The lesion involves the leg and arm · the photograph was taken at a distance · the contributor is a male aged 18–29: 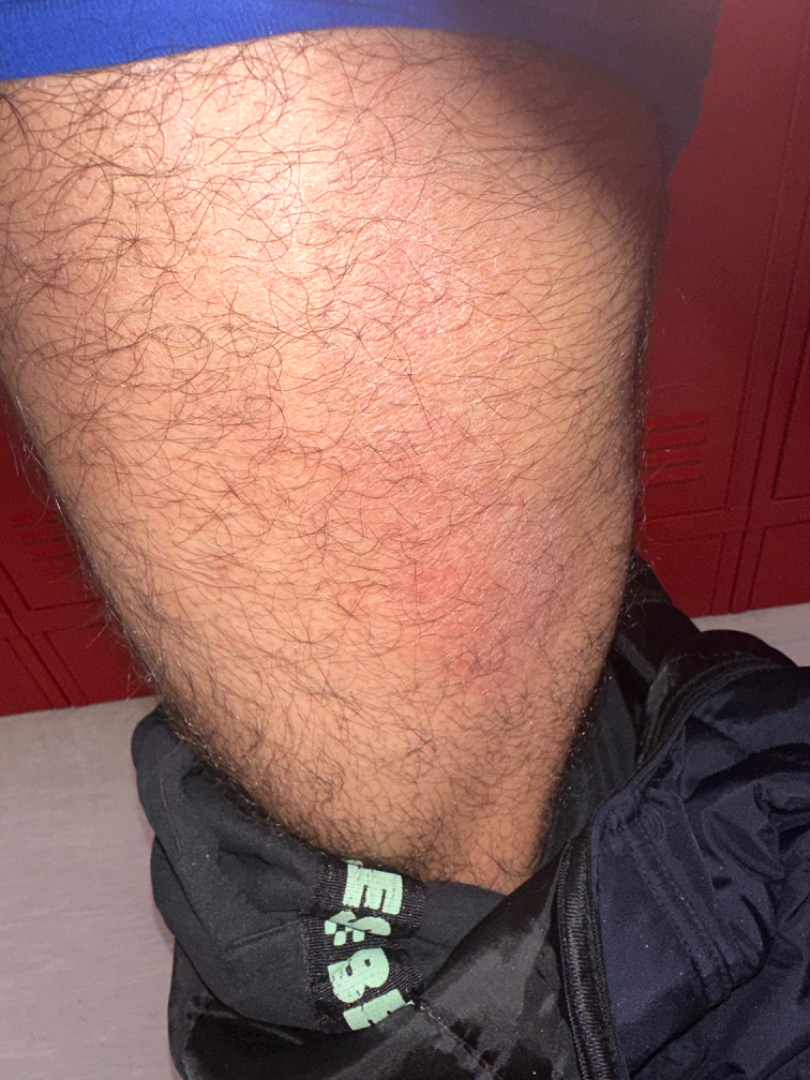Reported duration is one to three months. Reported lesion symptoms include bleeding, itching and enlargement. Texture is reported as rough or flaky. Skin tone: Fitzpatrick skin type II; non-clinician graders estimated Monk skin tone scale 3 (US pool) or 4 (India pool). On dermatologist assessment of the image, the leading impression is Acute and chronic dermatitis; an alternative is Xerosis; also raised was Eczema; possibly Irritant Contact Dermatitis.